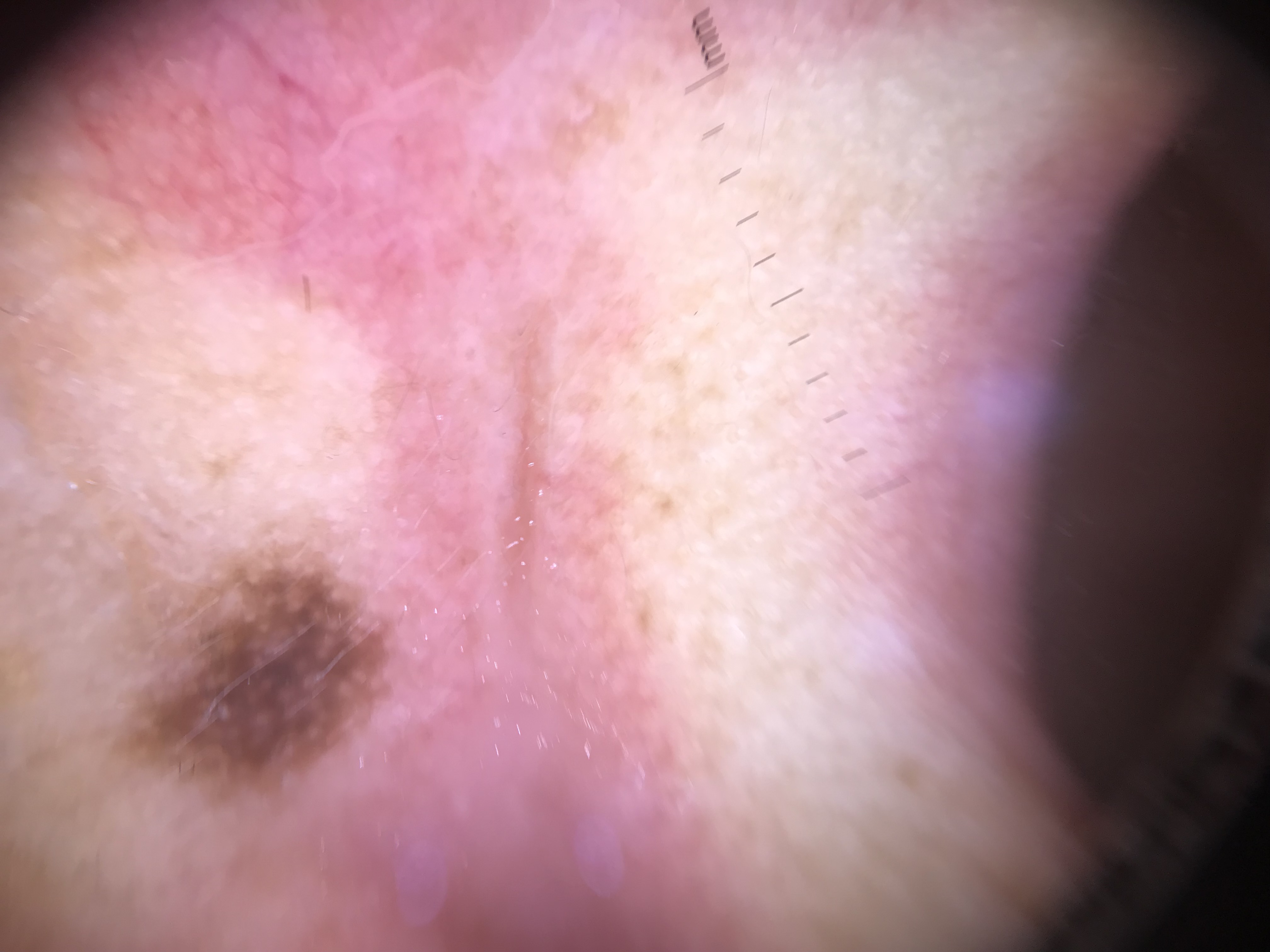– diagnosis: acral dysplastic junctional nevus (expert consensus)